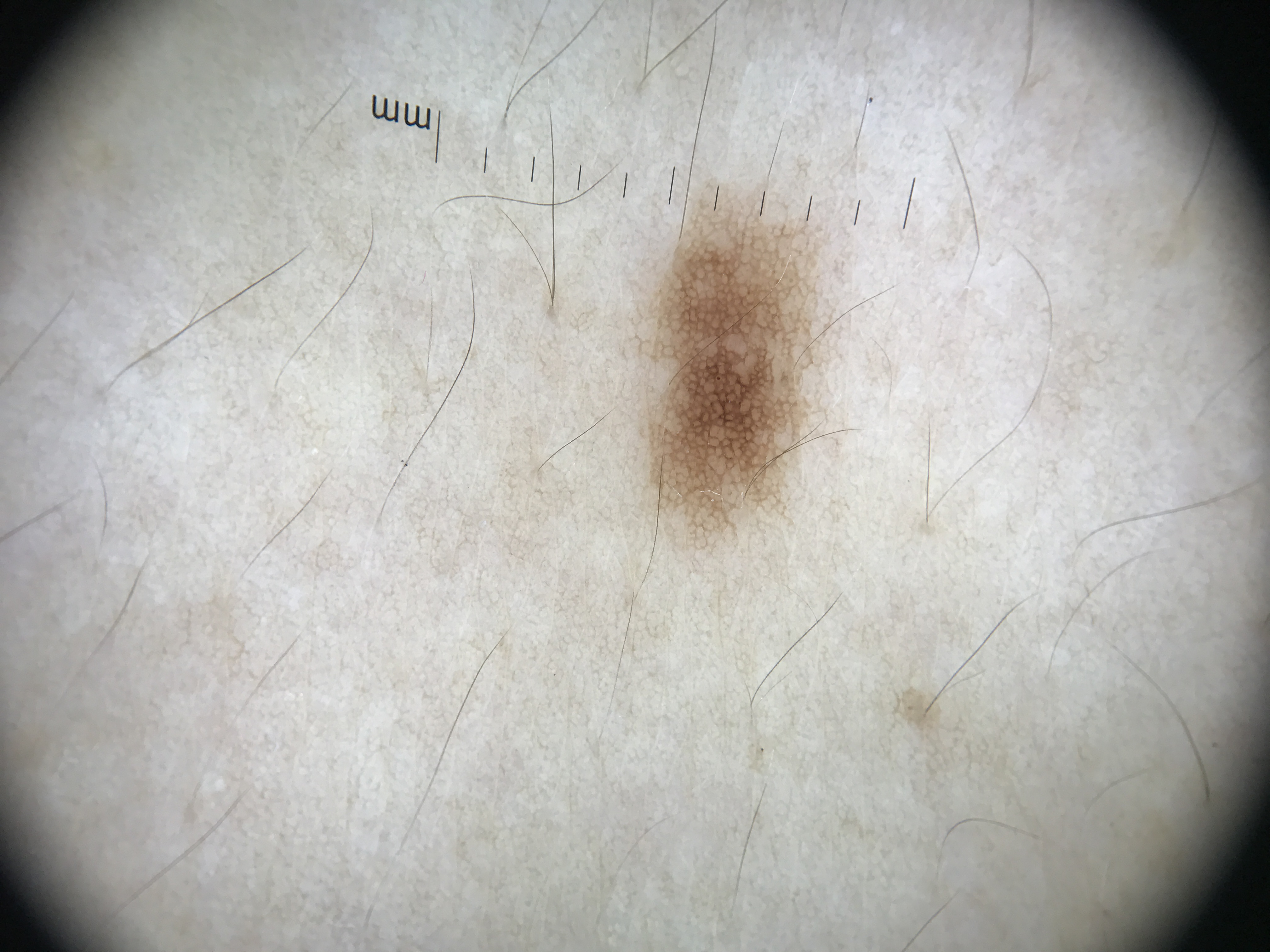Case:
A dermatoscopic image of a skin lesion. This is a banal lesion.
Impression:
Diagnosed as a junctional nevus.